A dermatoscopic image of a skin lesion — 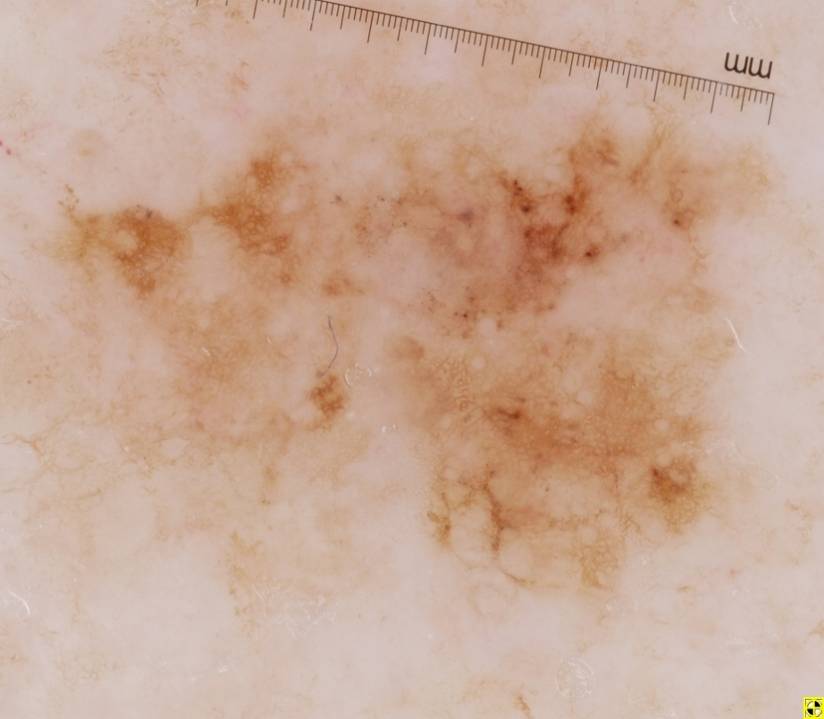Lesion location: [51, 85, 762, 592]. The lesion occupies roughly 36% of the field. Dermoscopic assessment notes globules, streaks, and pigment network. On biopsy, the diagnosis was a melanoma.